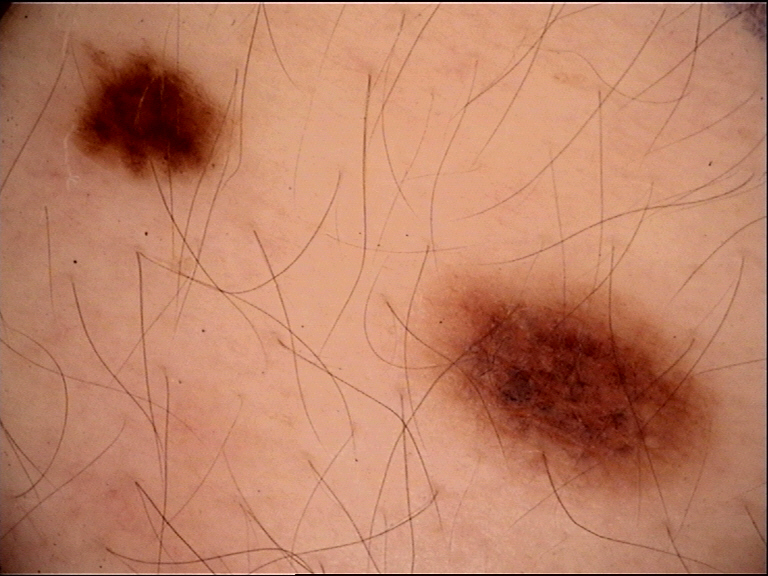imaging: dermatoscopy
label: dysplastic junctional nevus (expert consensus)